A dermoscopic close-up of a skin lesion.
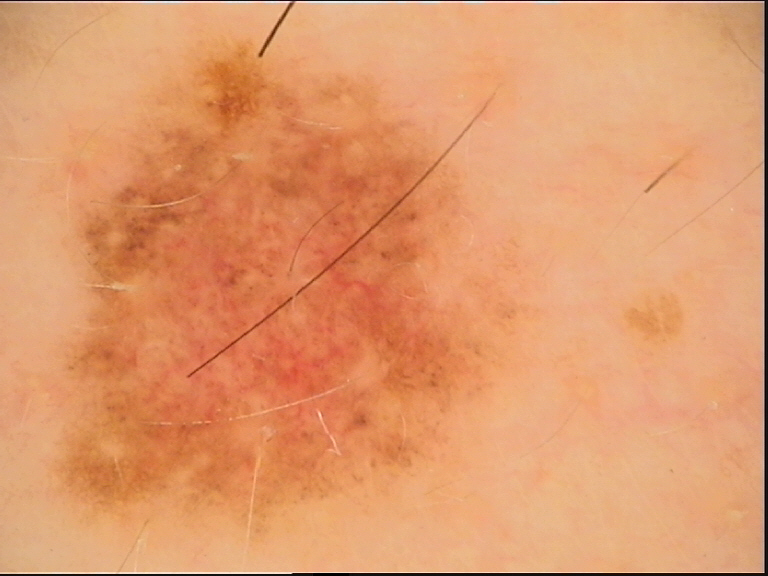Q: What is the diagnosis?
A: dysplastic junctional nevus (expert consensus)